The patient considered this a pigmentary problem · the leg is involved · texture is reported as raised or bumpy · Fitzpatrick phototype IV; lay graders estimated Monk skin tone scale 5 or 7 (two reviewer pools disagreed) · the condition has been present for less than one week · the patient is 18–29, female · symptoms reported: itching · an image taken at an angle.
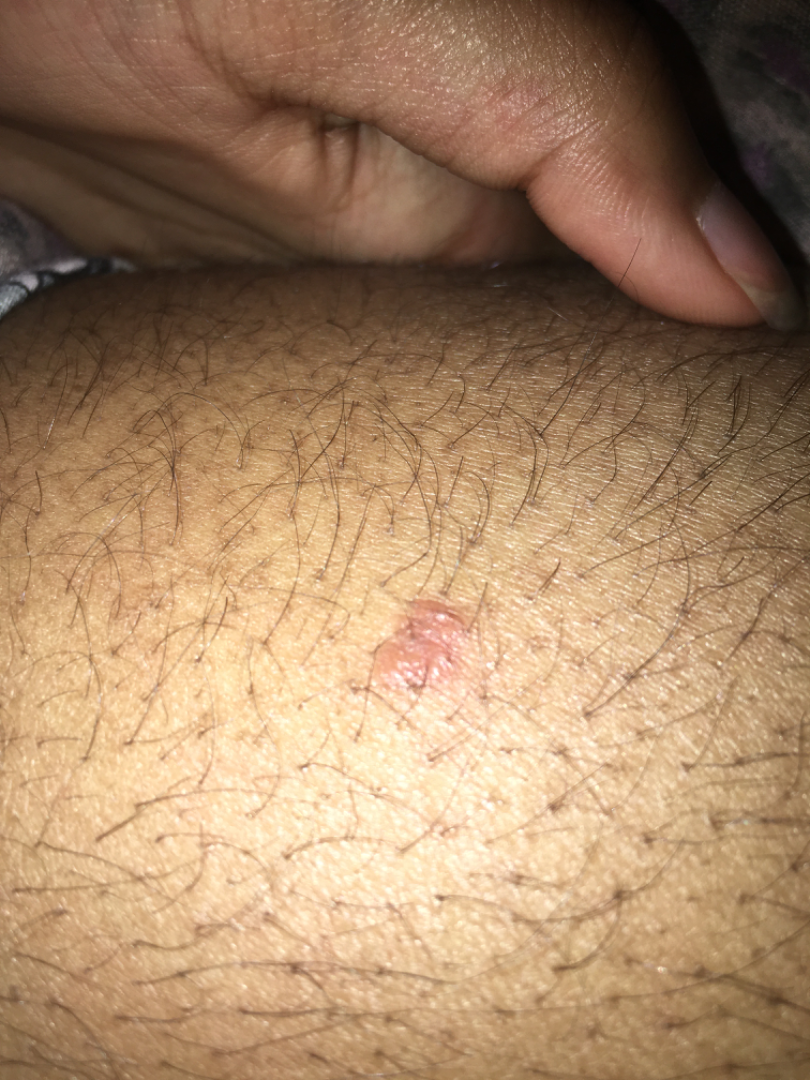differential:
  tied_lead:
    - Keratosis
    - Verruca vulgaris
    - Skin cancer